The contributor is 18–29, male. The condition has been present for about one day. The patient also reports fever, fatigue and chills. The patient reported no relevant symptoms from the lesion. The front of the torso, head or neck and back of the torso are involved. The contributor reports the lesion is flat. This image was taken at an angle.
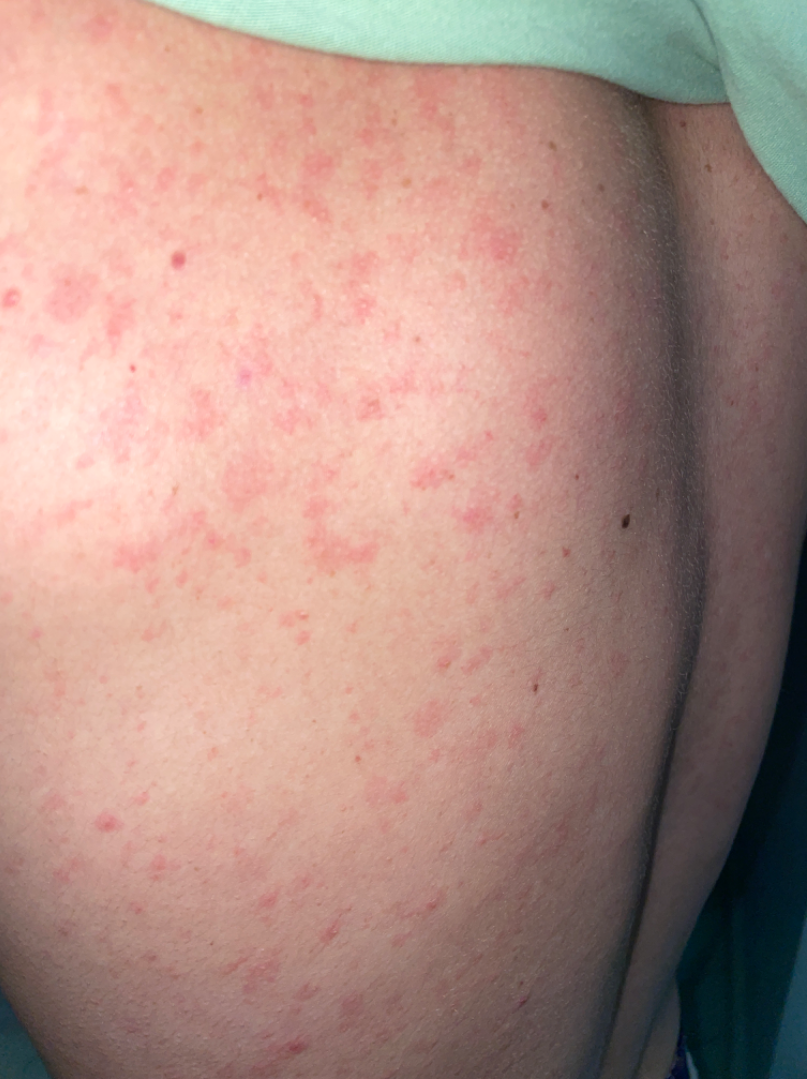Impression:
On dermatologist assessment of the image, the favored diagnosis is Drug Rash; also consider Viral Exanthem.